The photograph was taken at a distance; the patient reported no systemic symptoms; the patient is 60–69, female; the patient considered this a rash; the palm, front of the torso, arm and head or neck are involved; the patient indicates the lesion is raised or bumpy:
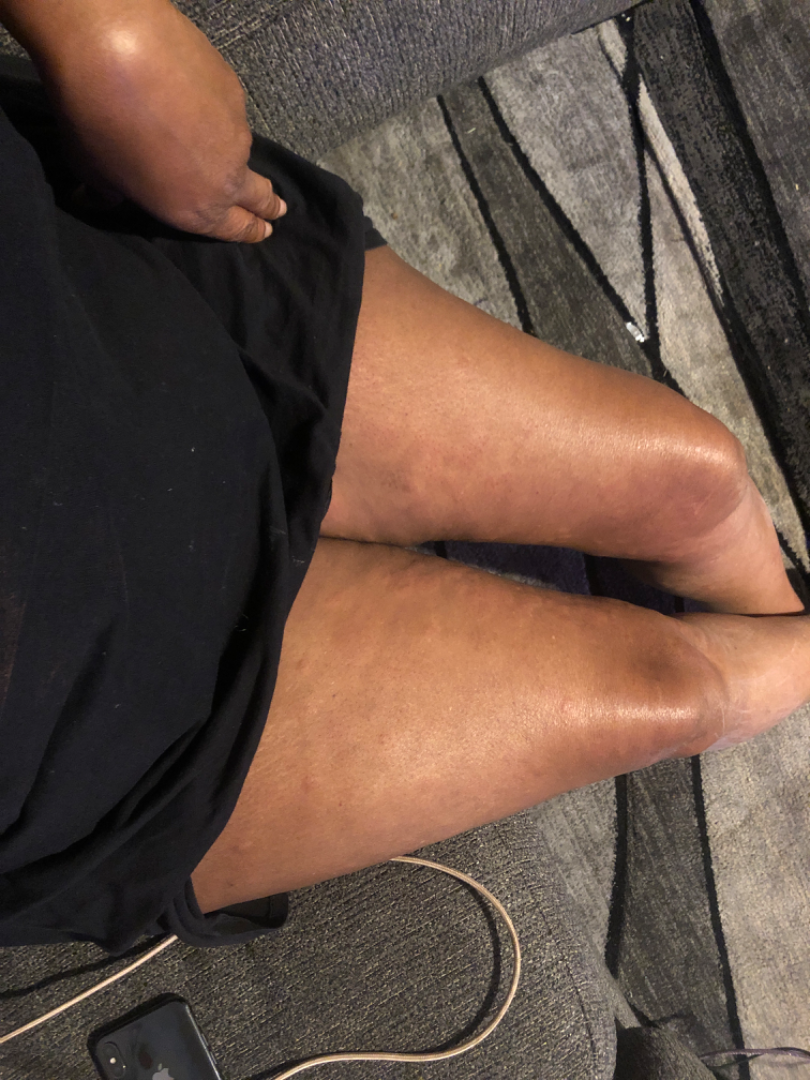dermatologist impression = in keeping with Urticaria.